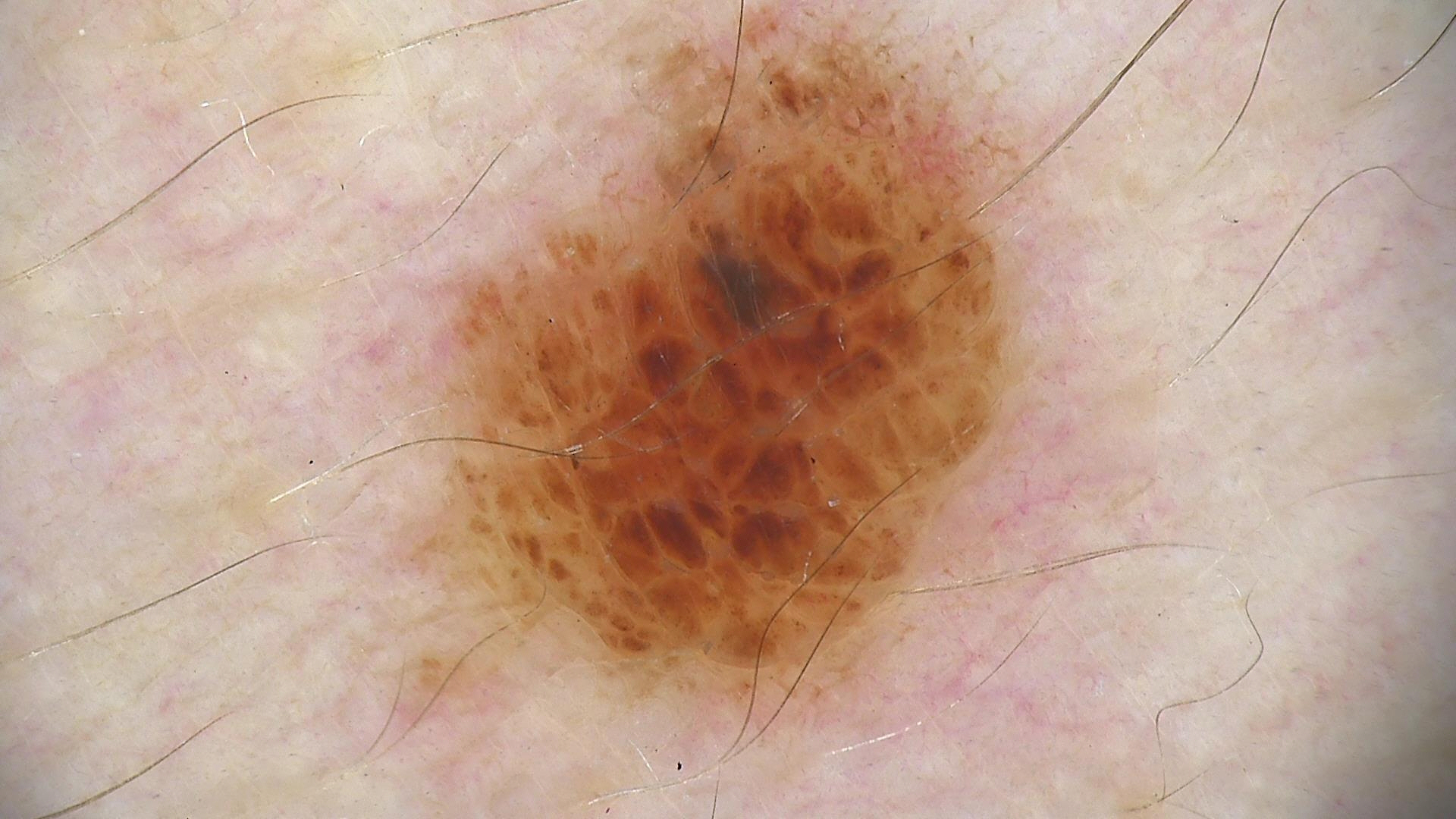A dermoscopic image of a skin lesion. The diagnosis was a compound nevus.